A skin lesion imaged with a dermatoscope:
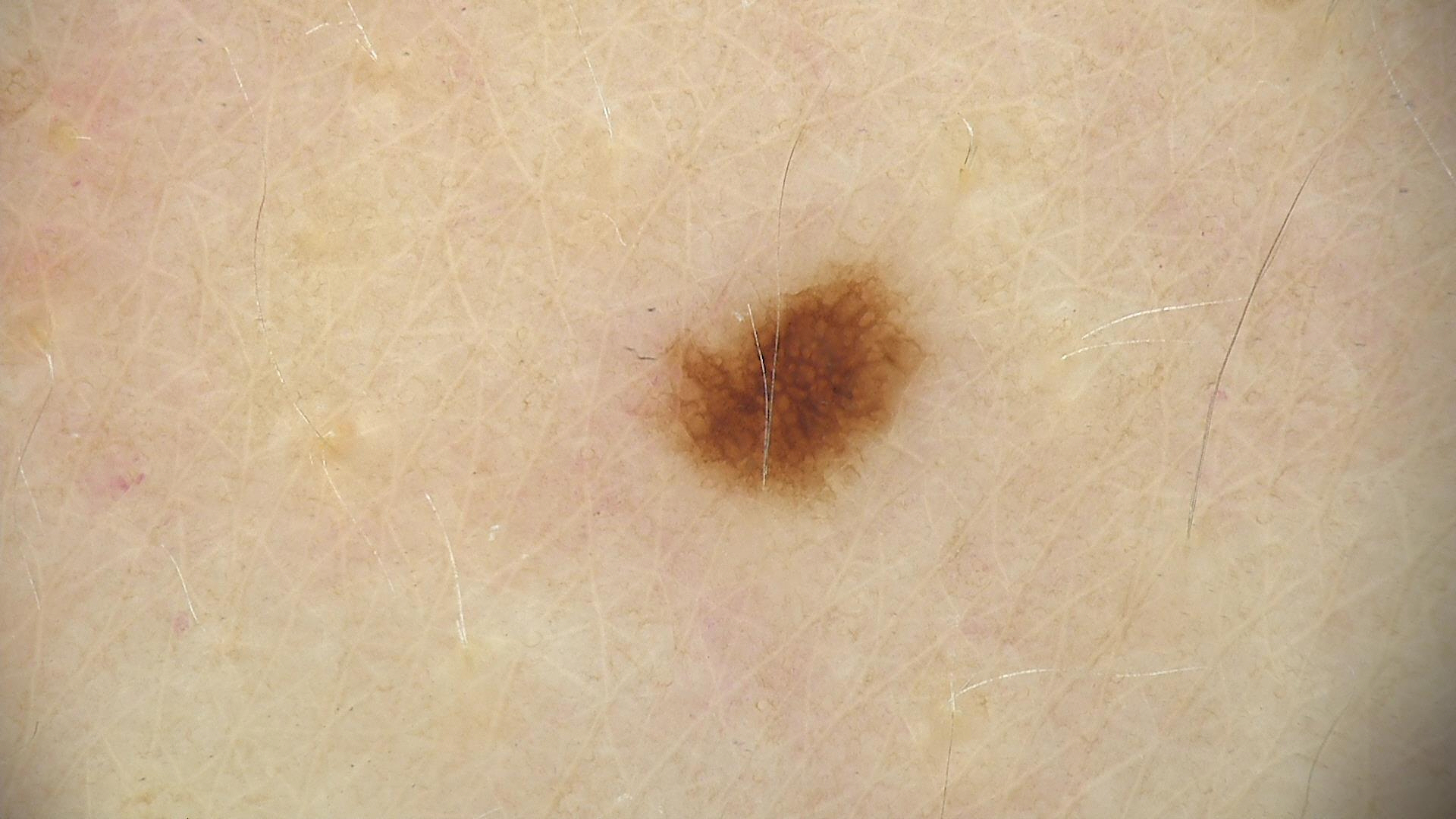The diagnostic label was a dysplastic junctional nevus.